The lesion is associated with itching, bothersome appearance and pain. The lesion is described as fluid-filled, raised or bumpy and rough or flaky. This image was taken at a distance. Located on the palm and back of the hand. Self-categorized by the patient as a rash — 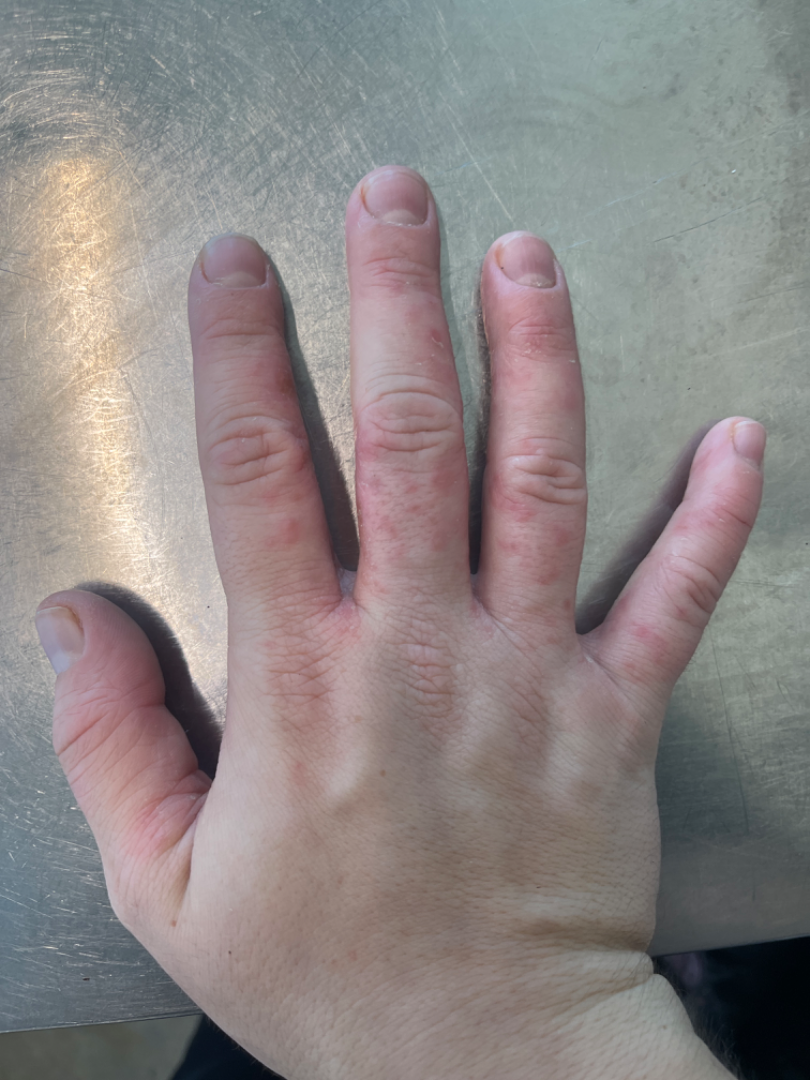Review: Three dermatologists independently reviewed the case: favoring Eczema; the differential also includes Irritant Contact Dermatitis; also raised was Scabies.